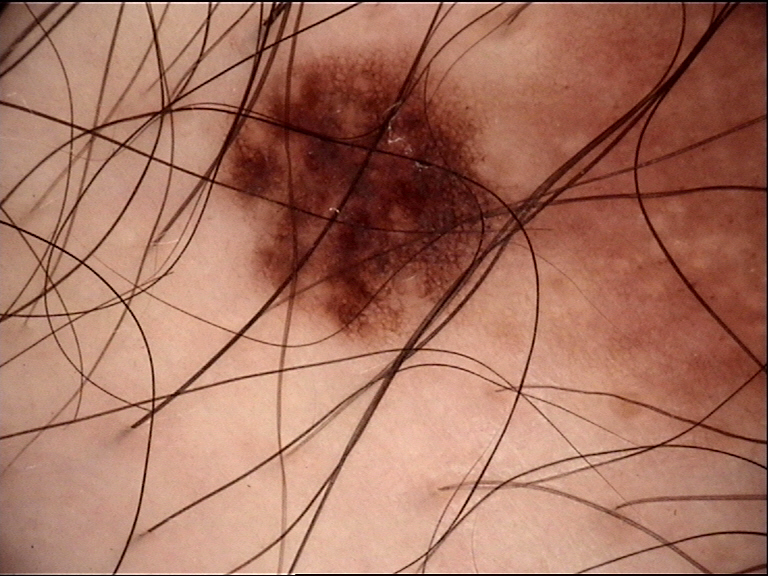A skin lesion imaged with a dermatoscope.
Diagnosed as a dysplastic junctional nevus.